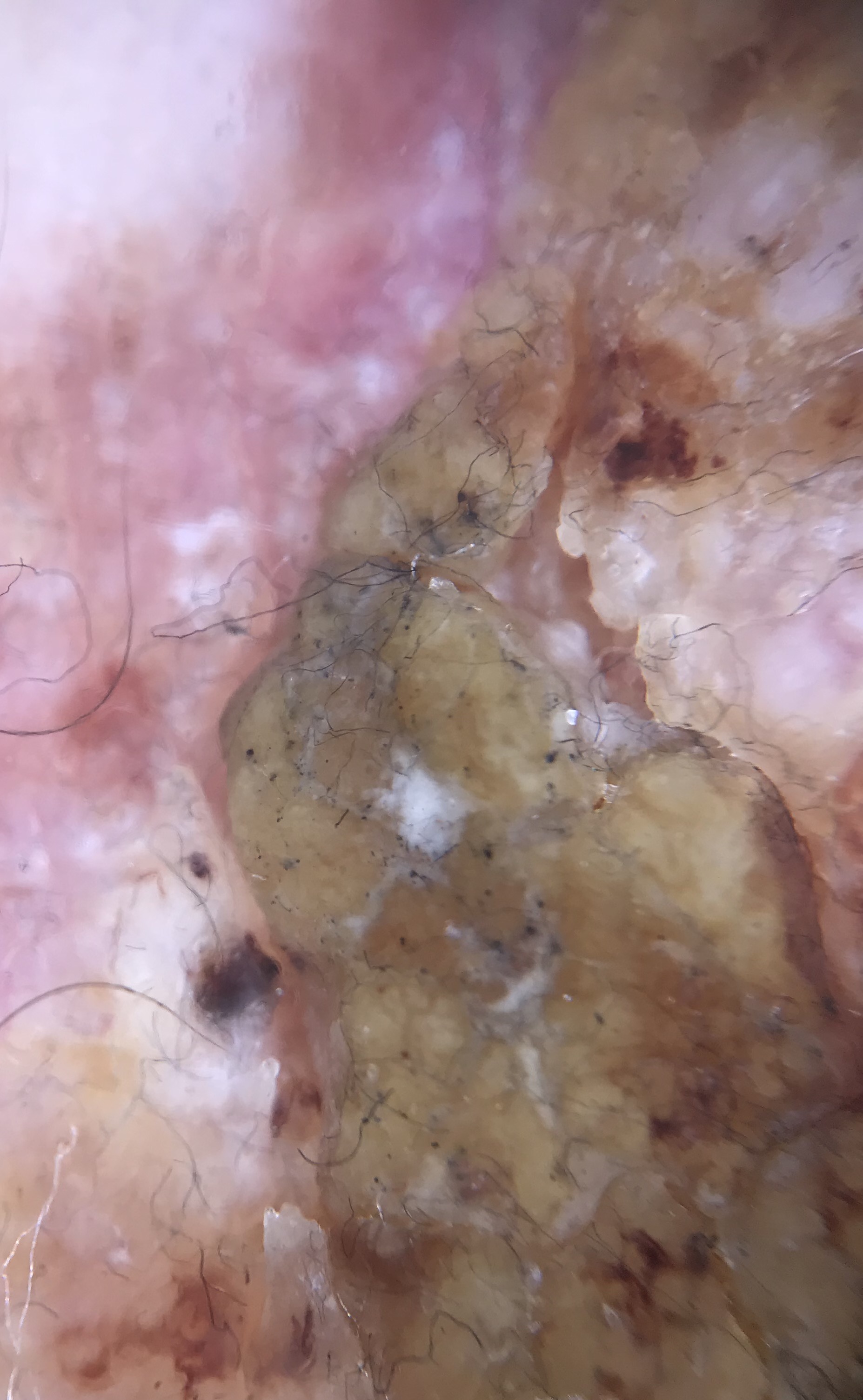A dermoscopic image of a skin lesion. Histopathologically confirmed as a squamous cell carcinoma.